The lesion involves the leg and arm · an image taken at an angle: 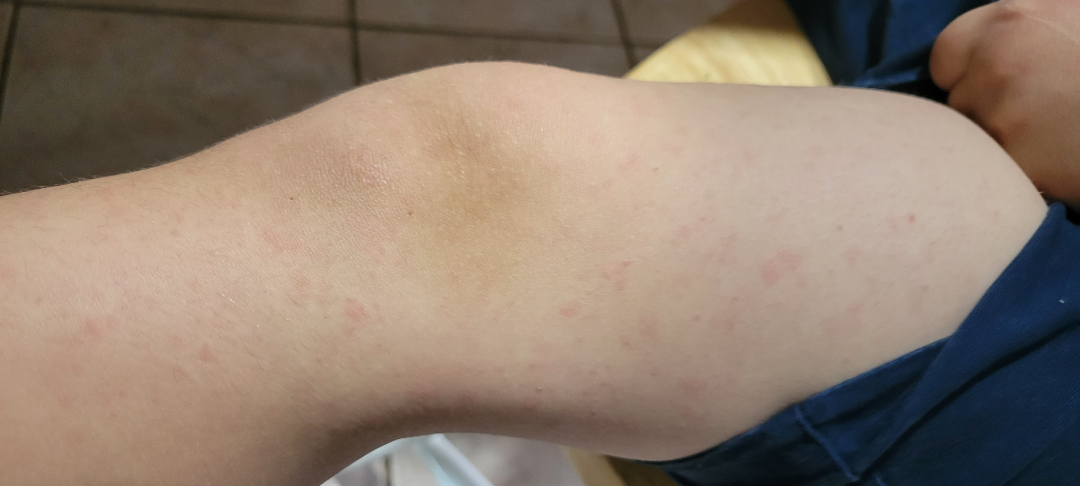assessment = ungradable on photographic review | patient's own categorization = a rash | history = about one day | reported symptoms = none reported | associated systemic symptoms = fever | texture = flat.